The affected area is the arm; the contributor is a female aged 50–59; a close-up photograph:
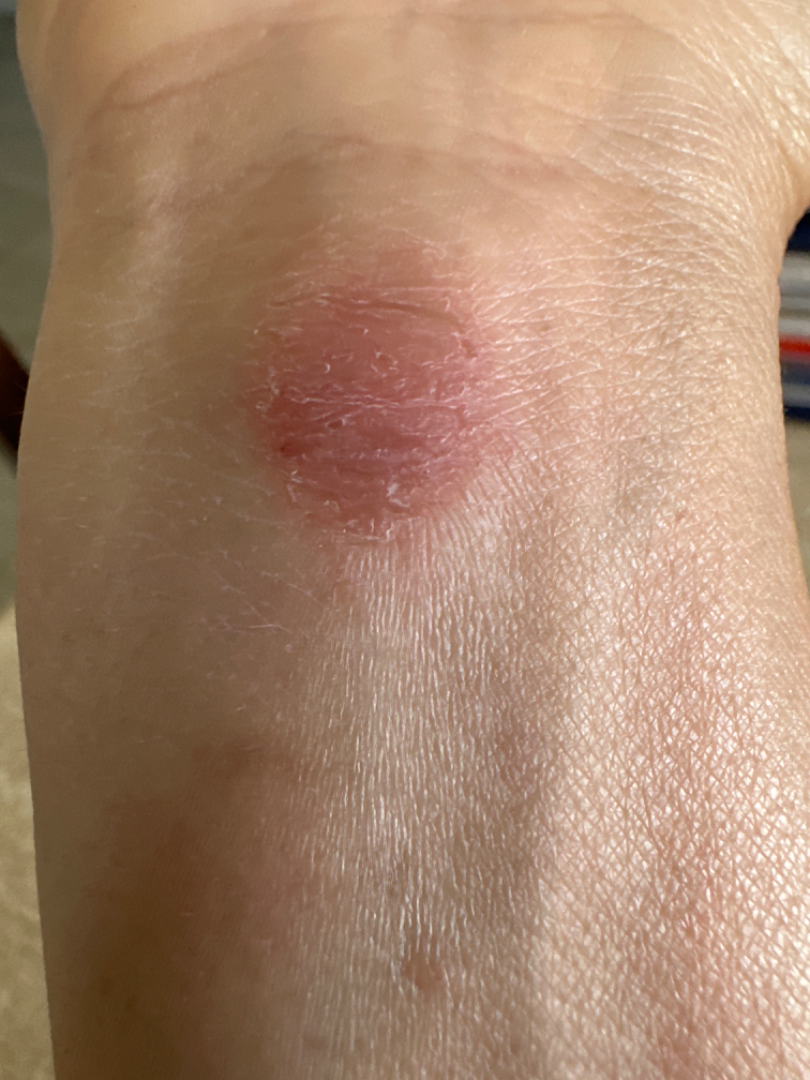Q: What conditions are considered?
A: the favored diagnosis is Allergic Contact Dermatitis